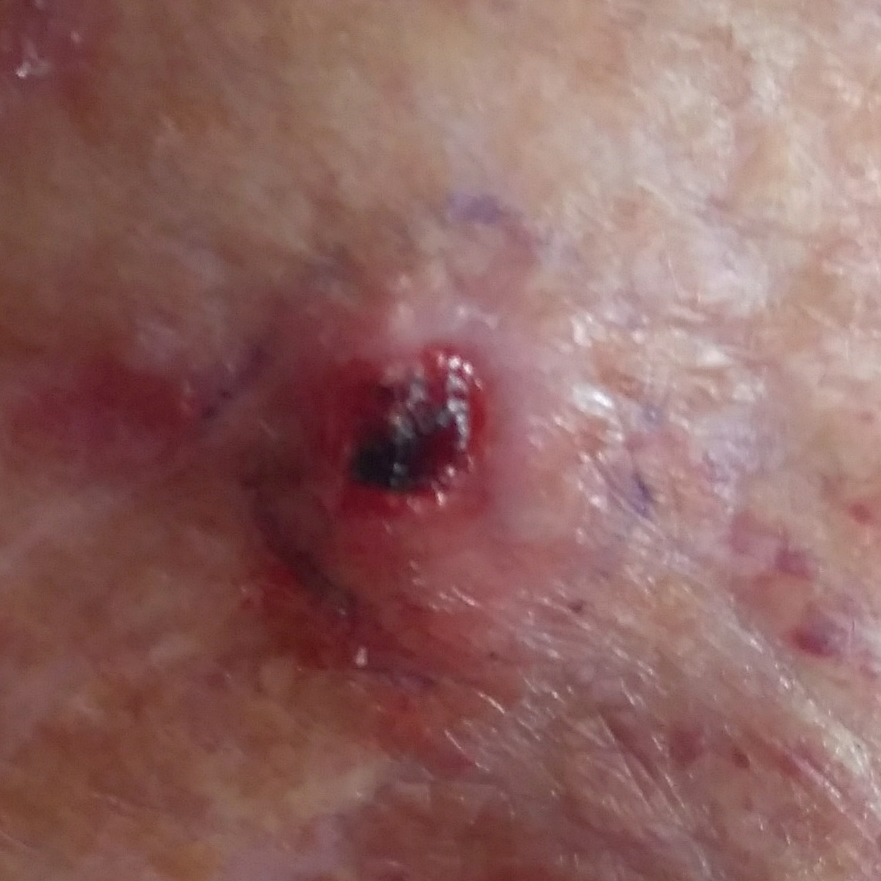Conclusion:
Histopathologically confirmed as a basal cell carcinoma.